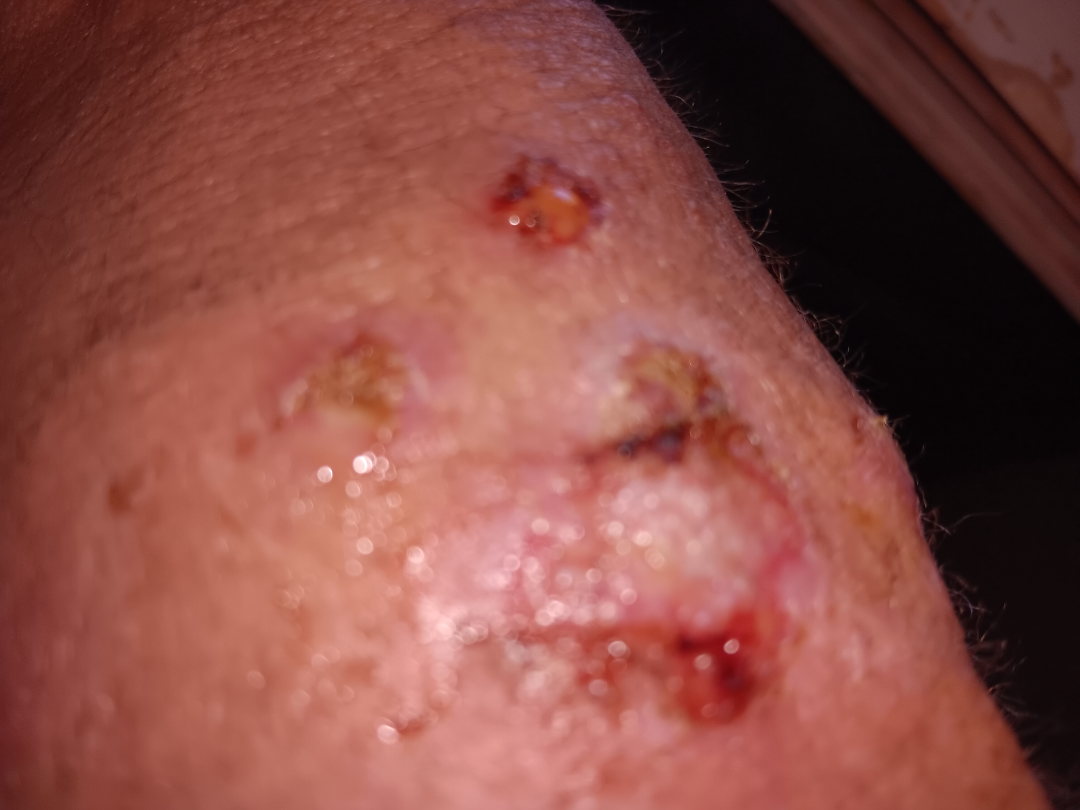Findings:
• patient describes the issue as: a rash
• body site: leg, head or neck, arm and back of the hand
• present for: more than one year
• associated systemic symptoms: fever, fatigue, chills, joint pain and shortness of breath
• lesion texture: fluid-filled, rough or flaky and raised or bumpy
• shot type: close-up
• assessment: the differential, in no particular order, includes Abrasion, scrape, or scab and Ecthyma; an alternative is Impetigo; a more distant consideration is Mycetoma